Female contributor, age 18–29. Located on the leg and arm. This image was taken at an angle.
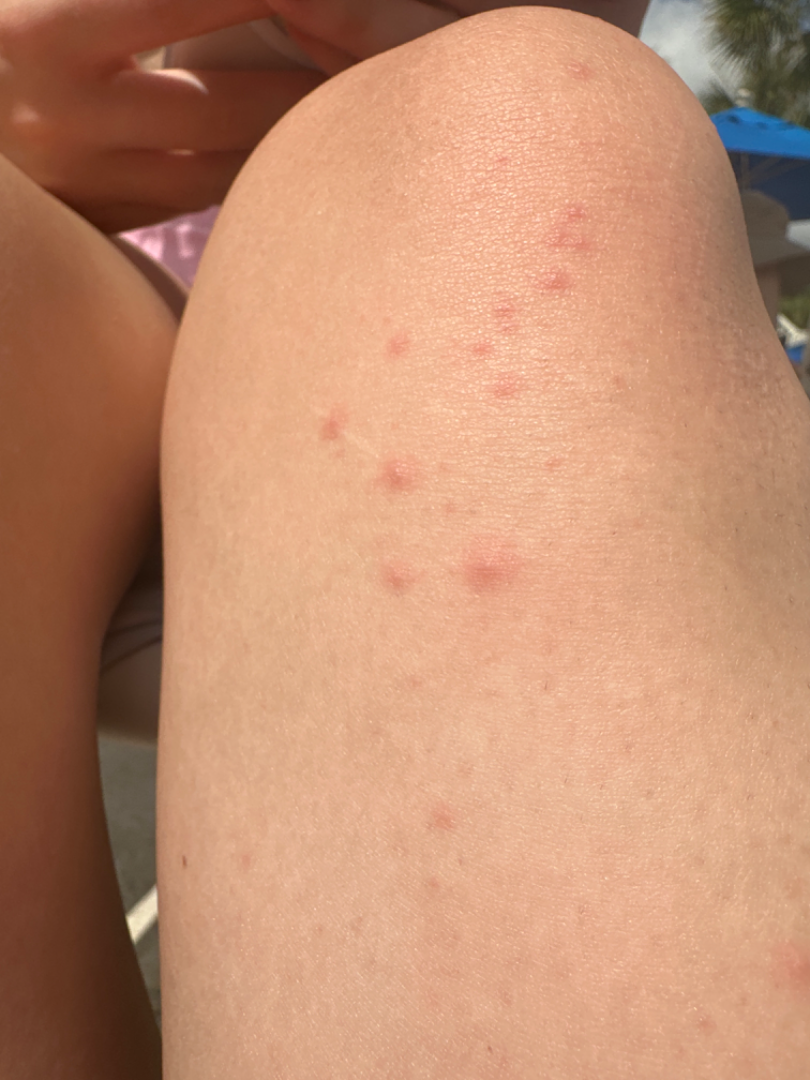Background: The lesion is described as fluid-filled. The patient reported no systemic symptoms. Self-categorized by the patient as a rash. The condition has been present for about one day. Findings: On remote review of the image, in keeping with Folliculitis.